The photograph was taken at a distance. The contributor is a male aged 18–29. Located on the leg:
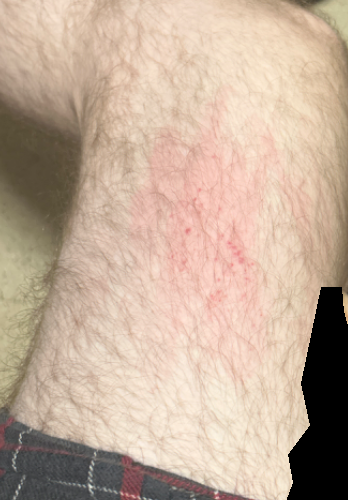Q: Could the case be diagnosed?
A: indeterminate from the photograph
Q: What is the lesion texture?
A: flat
Q: How long has this been present?
A: about one day
Q: How does the patient describe it?
A: a rash